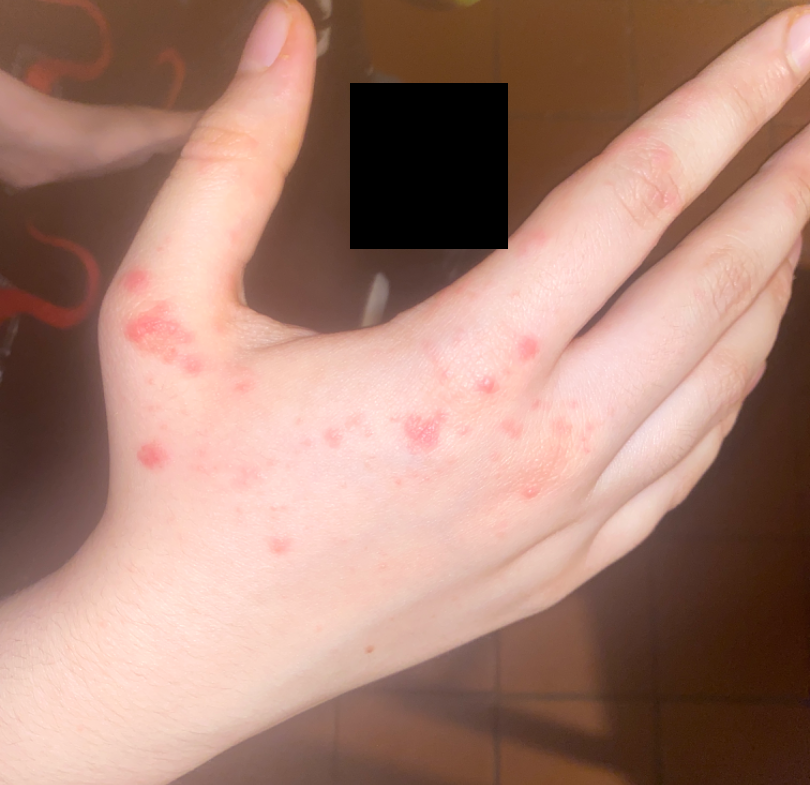Q: What is the differential diagnosis?
A: the differential is split between Impetigo, Molluscum Contagiosum and Allergic Contact Dermatitis